An image taken at an angle · present for one to four weeks · the lesion is described as raised or bumpy: 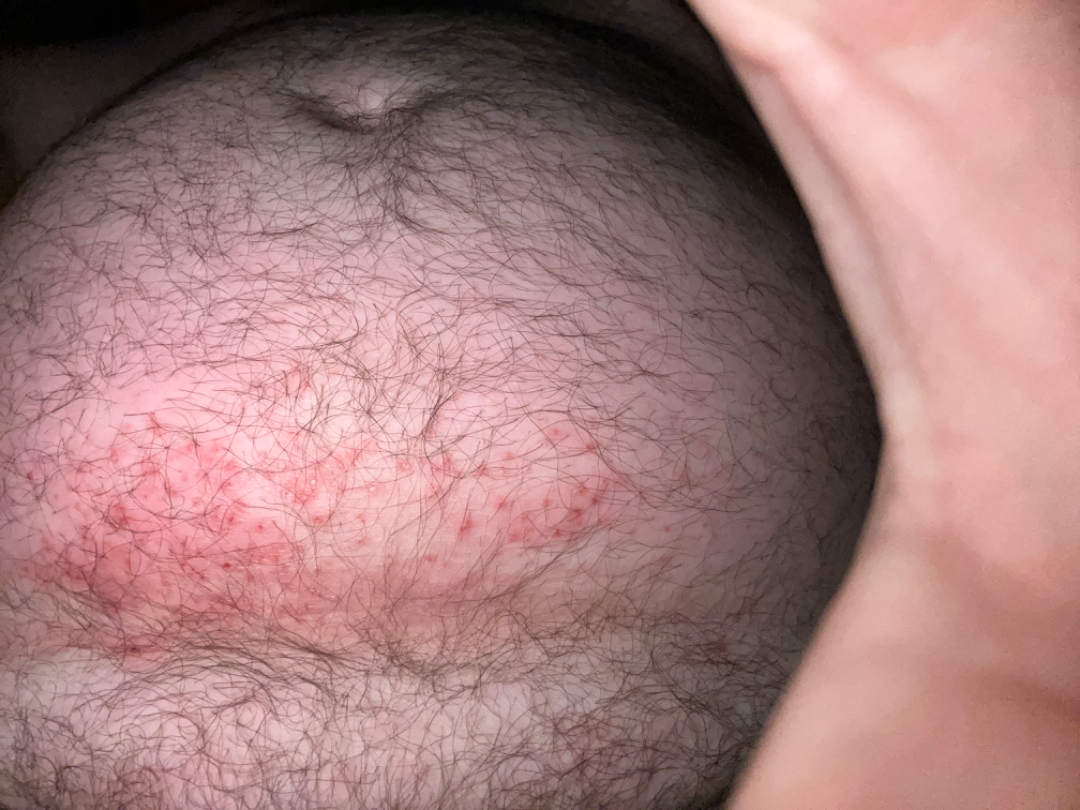On teledermatology review: the differential, in no particular order, includes Intertrigo and Eczema; a remote consideration is Allergic Contact Dermatitis.